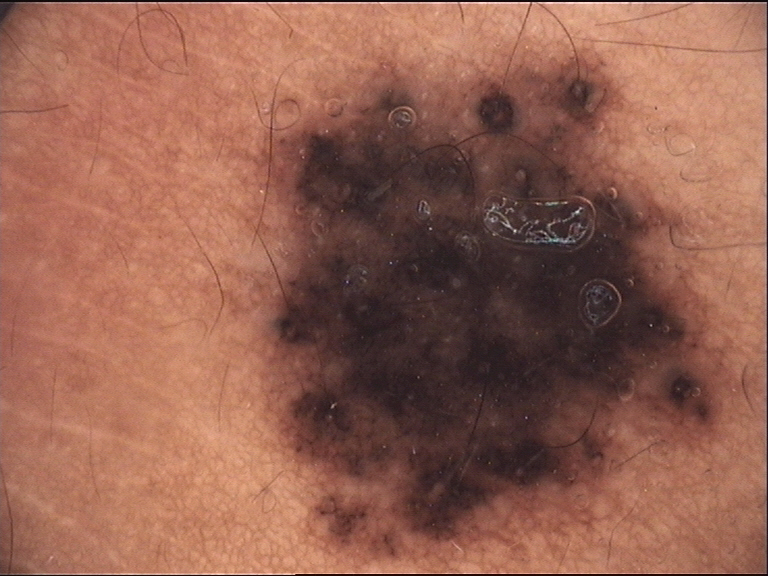Q: What is the diagnosis?
A: congenital dysplastic compound nevus (expert consensus)